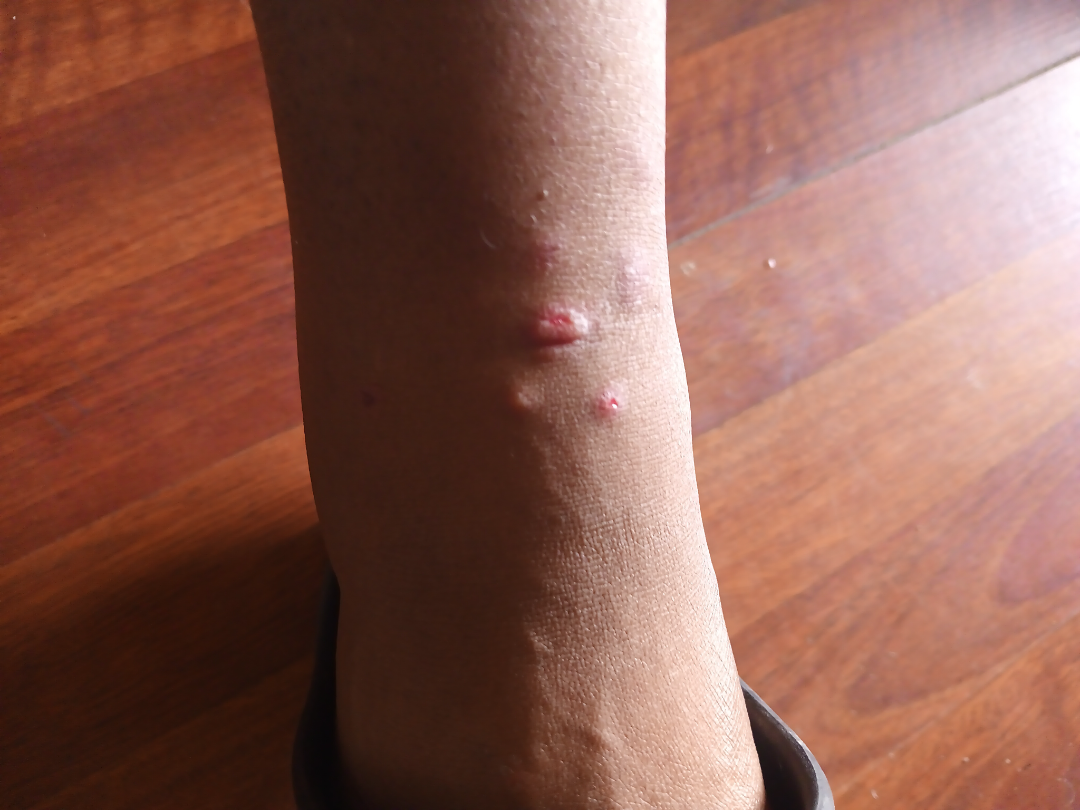{
  "skin_tone": {
    "monk_skin_tone": 2
  },
  "shot_type": "close-up",
  "differential": {
    "leading": [
      "Insect Bite"
    ]
  }
}